The lesion involves the arm, reported lesion symptoms include burning and itching, the contributor is a male aged 70–79, reported duration is one to four weeks, the photograph was taken at an angle:
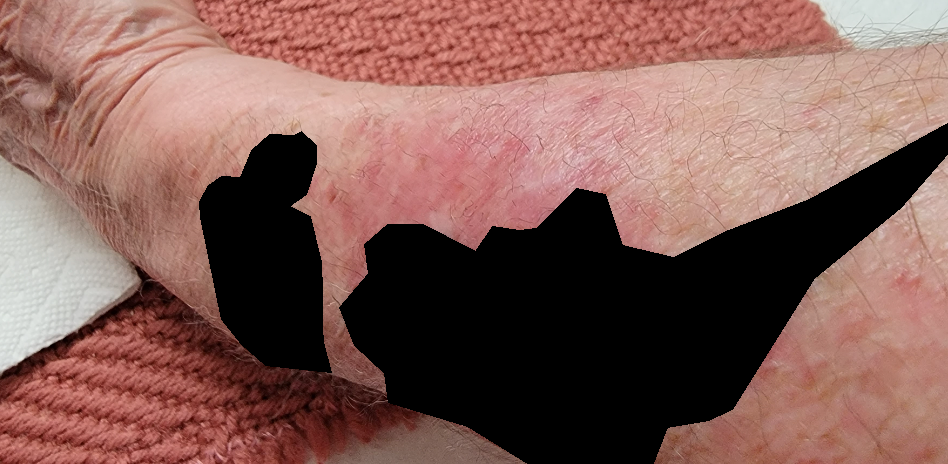Three dermatologists each reviewed the case: consistent with Eczema.